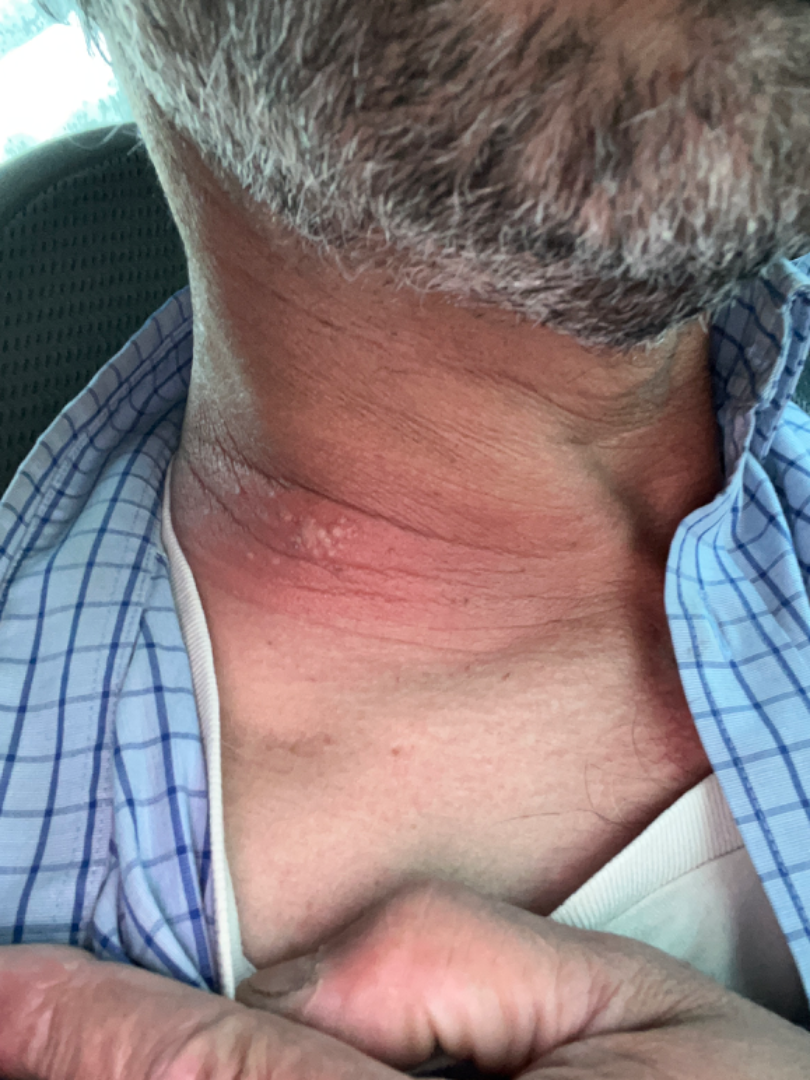  differential:
    leading:
      - Herpes Zoster
    considered:
      - Allergic Contact Dermatitis
      - Herpes Simplex